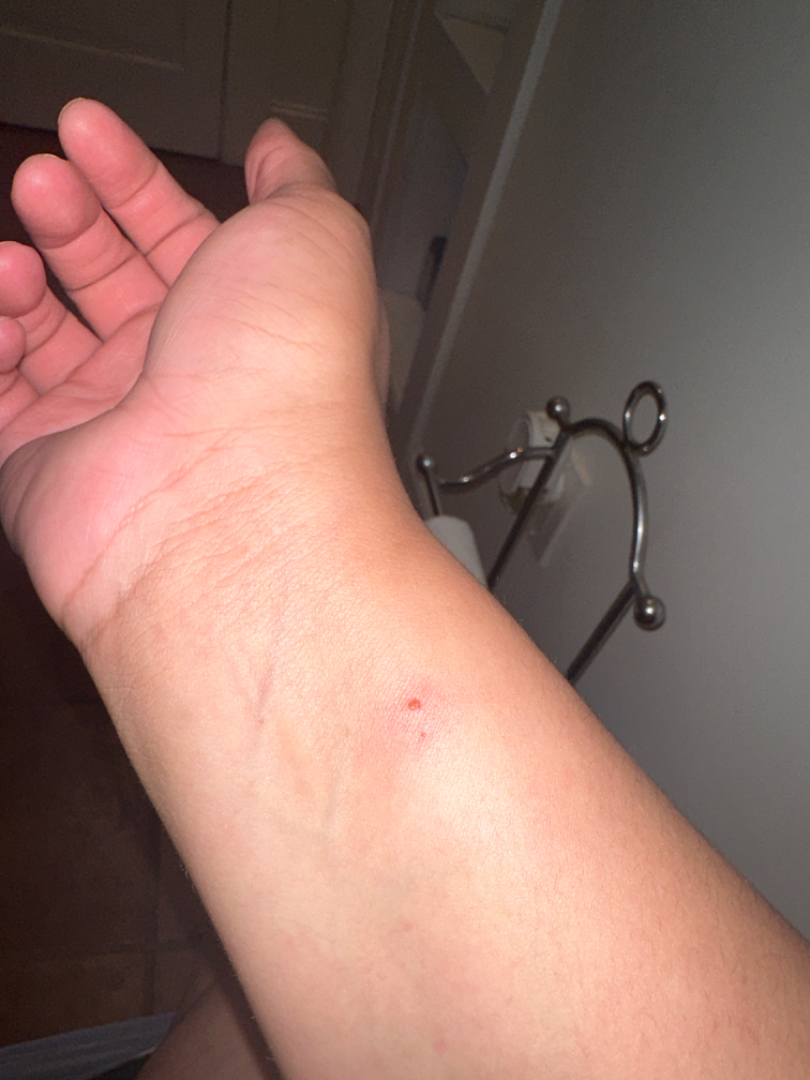The patient reports bothersome appearance, burning and itching. The patient considered this a rash. Female contributor, age 18–29. The patient reports the condition has been present for less than one week. The photo was captured at a distance. The front of the torso, leg and arm are involved. On teledermatology review, in keeping with Contact dermatitis.